An overview clinical photograph of a skin lesion · a male patient in their 70s · skin type II — 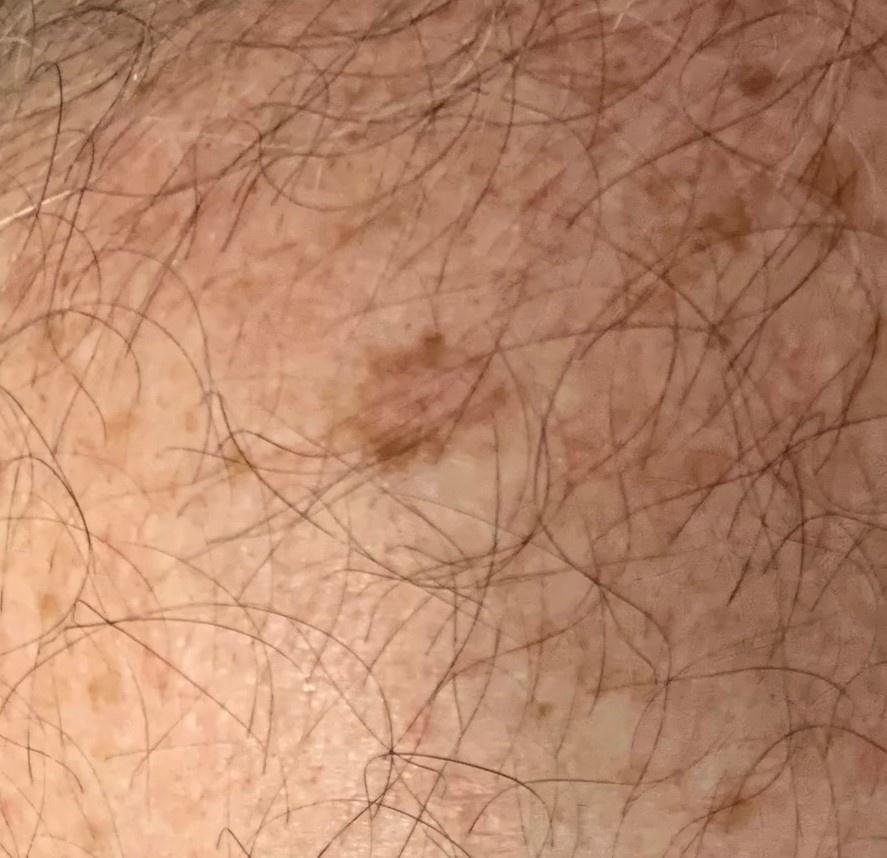The lesion was found on the trunk.
The biopsy diagnosis was an adnexal lesion — a basal cell carcinoma.